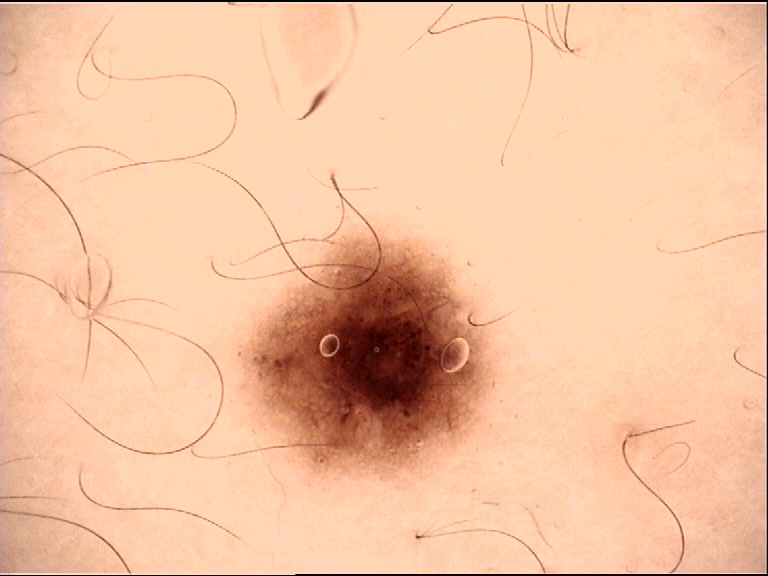A dermoscopic image of a skin lesion.
Classified as a dysplastic junctional nevus.